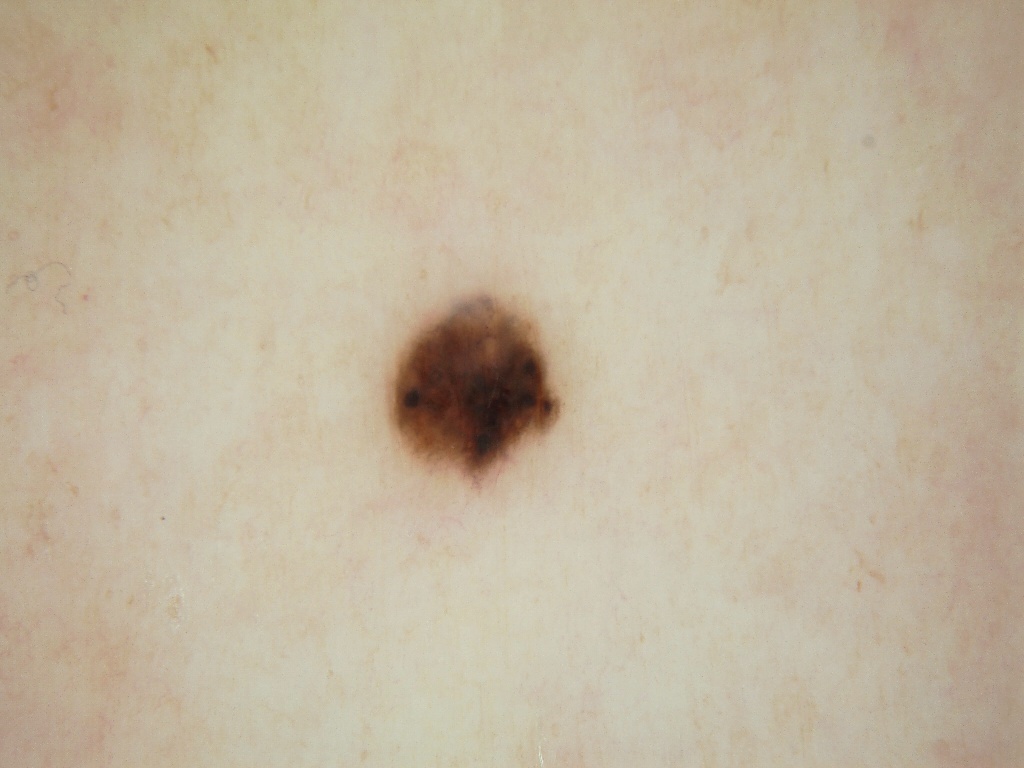Q: How was this image acquired?
A: dermatoscopic image of a skin lesion
Q: Who is the patient?
A: female, aged 48 to 52
Q: Where is the lesion located?
A: bbox=[385, 291, 560, 483]
Q: What dermoscopic features are not present?
A: globules, milia-like cysts, pigment network, streaks, and negative network
Q: How large is the lesion within the image?
A: small
Q: What did the assessment conclude?
A: a melanocytic nevus